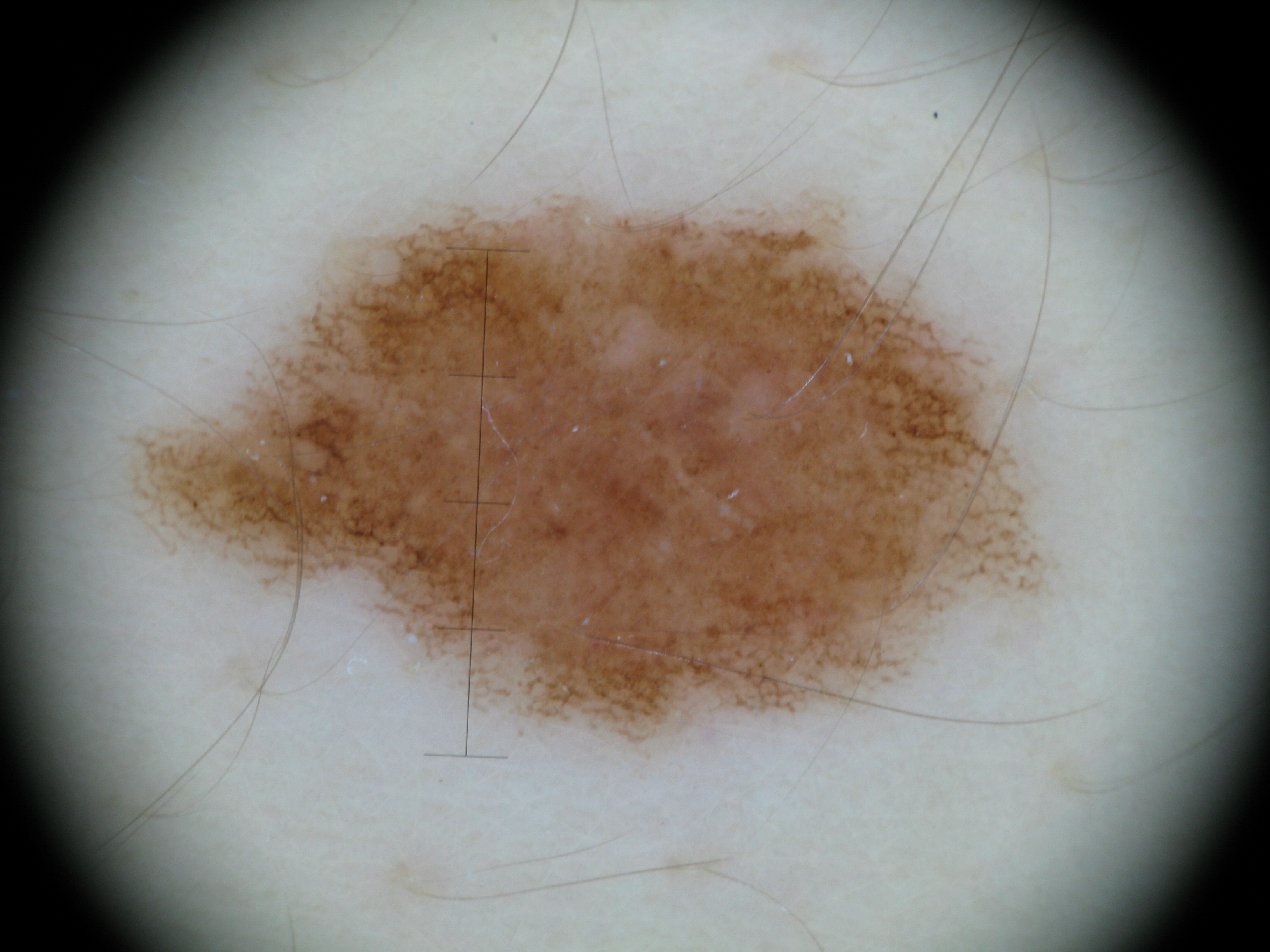| feature | finding |
|---|---|
| diagnostic label | dysplastic junctional nevus (expert consensus) |